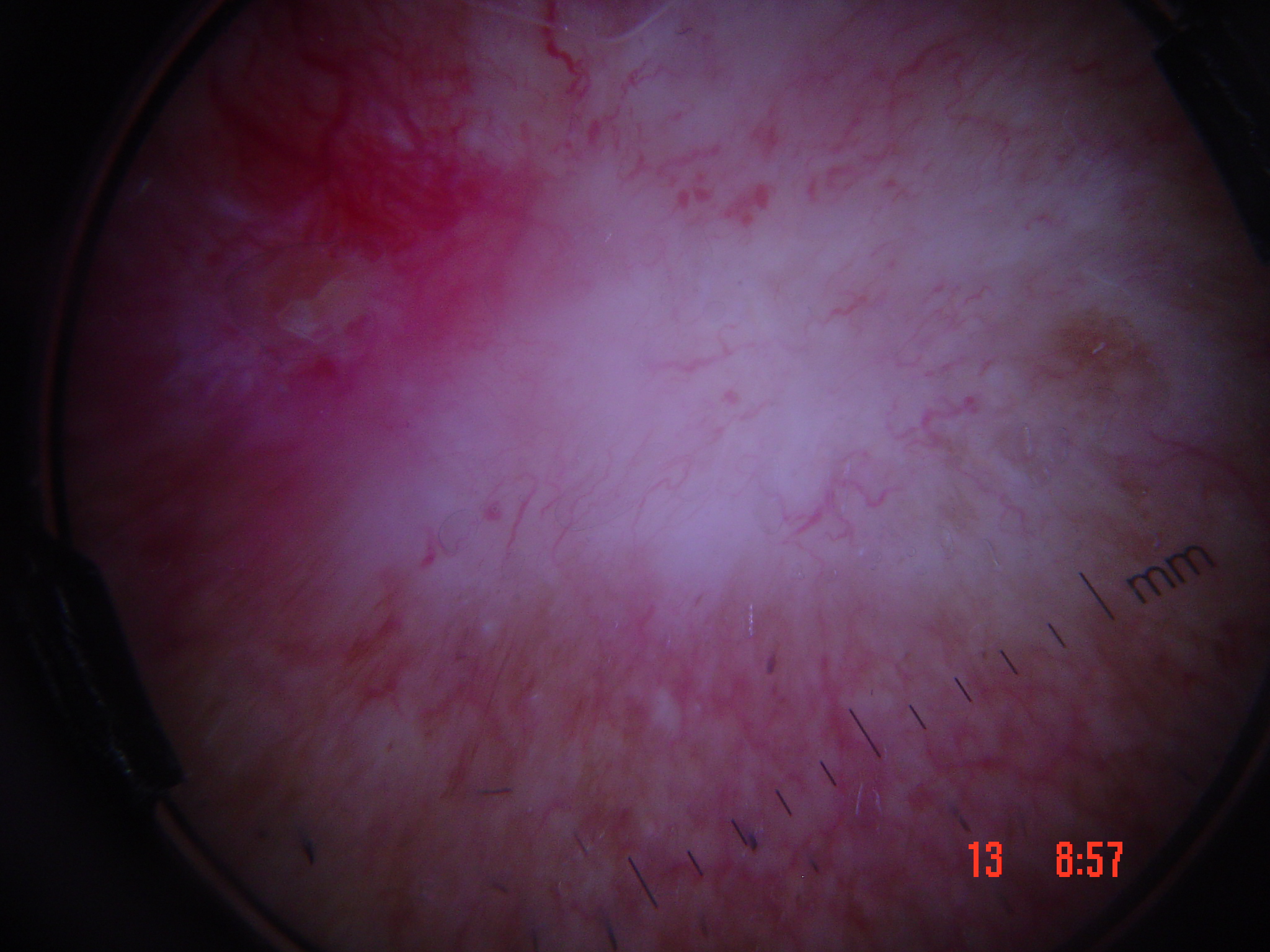Q: What is this lesion?
A: basal cell carcinoma (biopsy-proven)